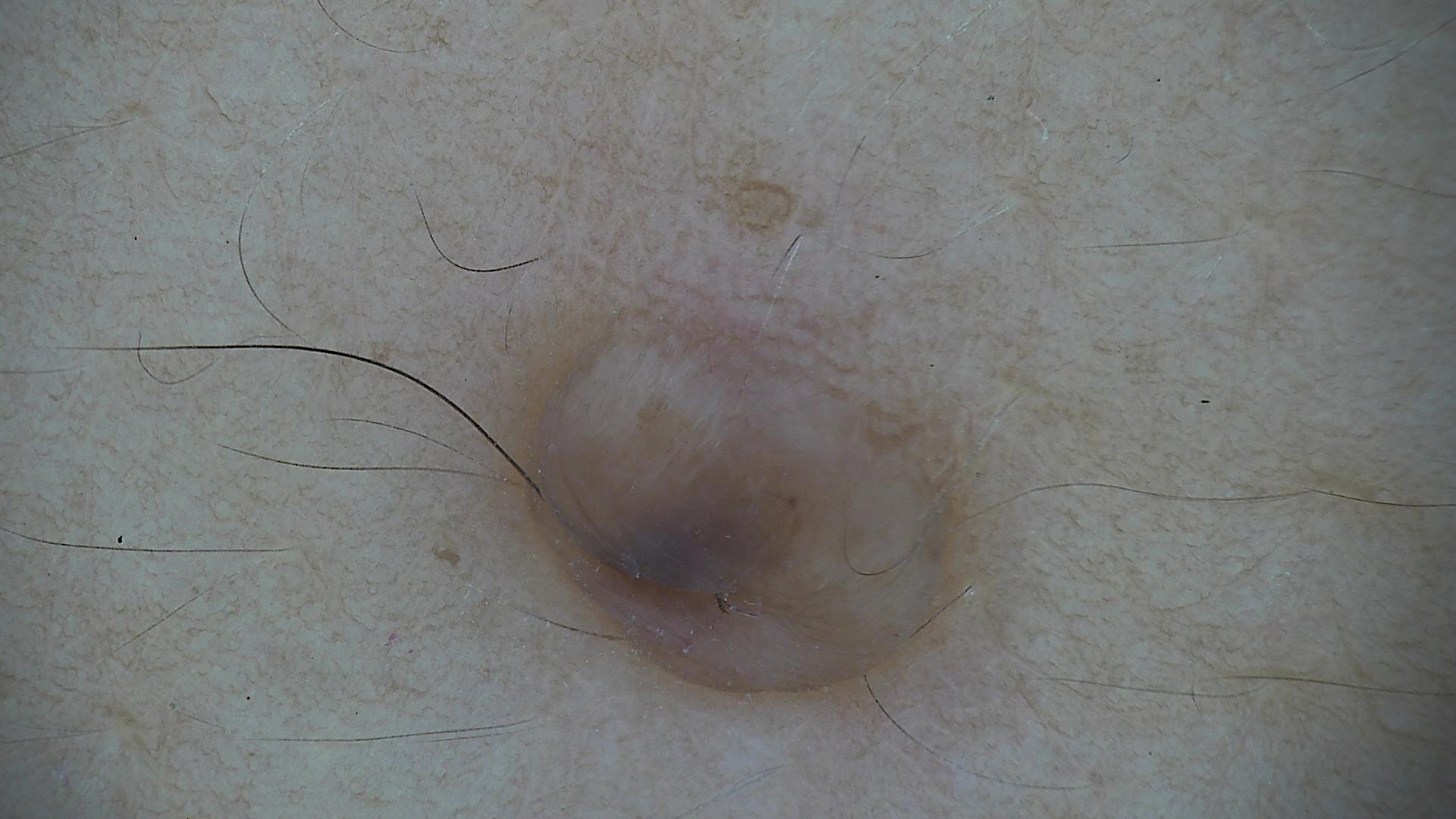Dermoscopy of a skin lesion.
The diagnosis was a banal lesion — a dermal nevus.